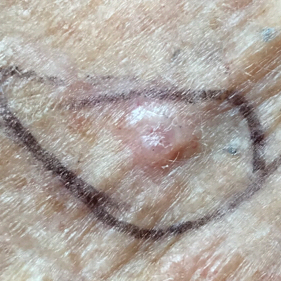A clinical photograph of a skin lesion. By the patient's account, the lesion is elevated and itches. The biopsy diagnosis was a basal cell carcinoma.